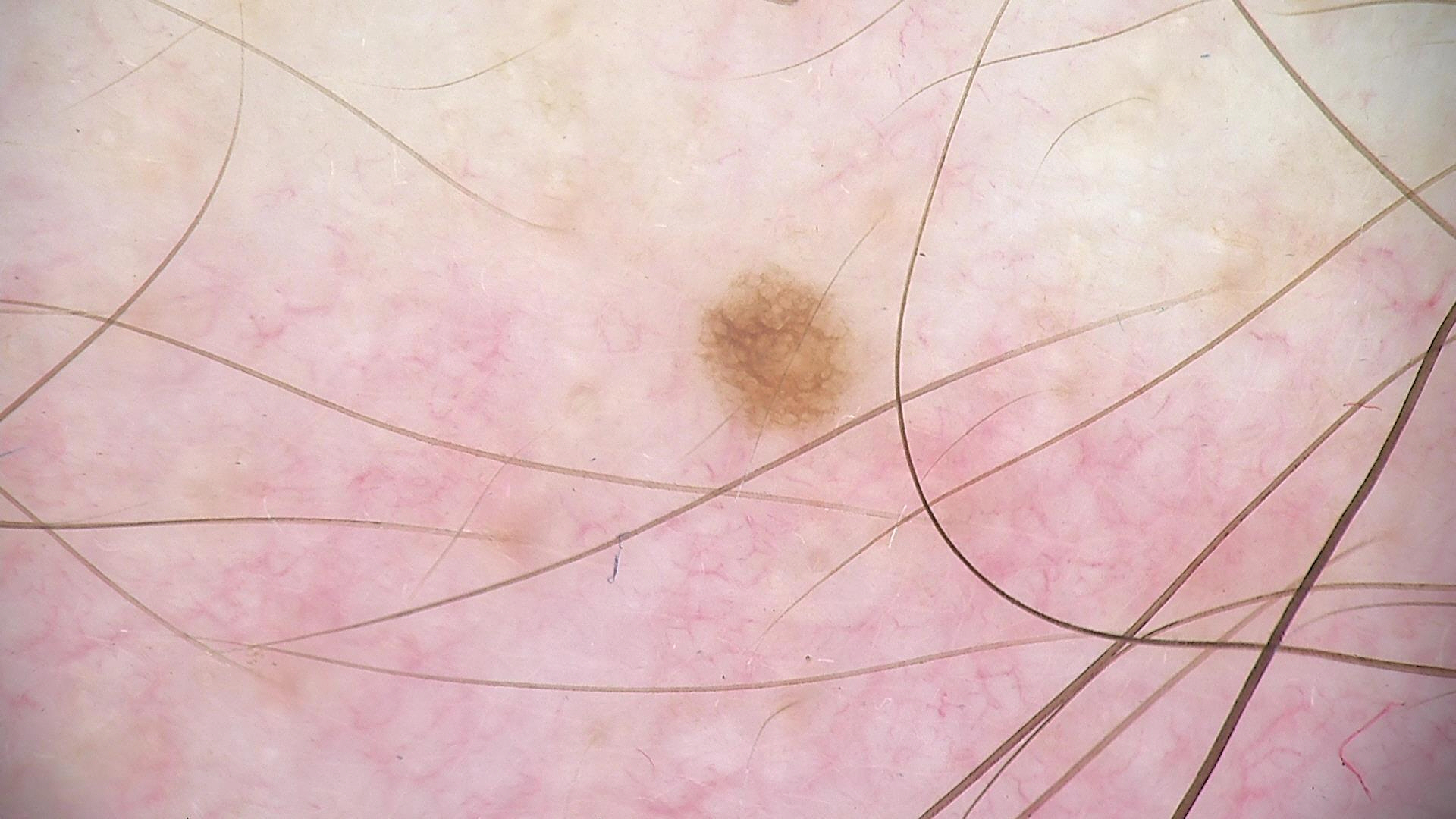A dermoscopic photograph of a skin lesion. The diagnostic label was a benign lesion — a dysplastic junctional nevus.